Located on the leg and arm. A close-up photograph. The patient indicates the condition has been present for three to twelve months. The patient considered this a rash: 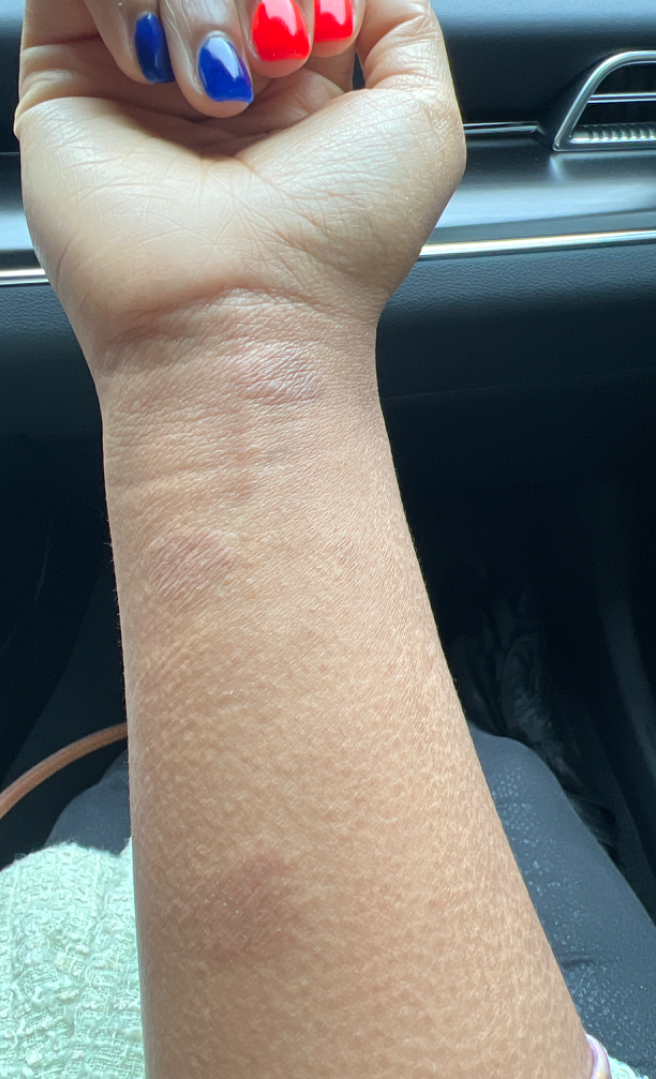Findings: Consistent with Eczema.